A close-up photograph.
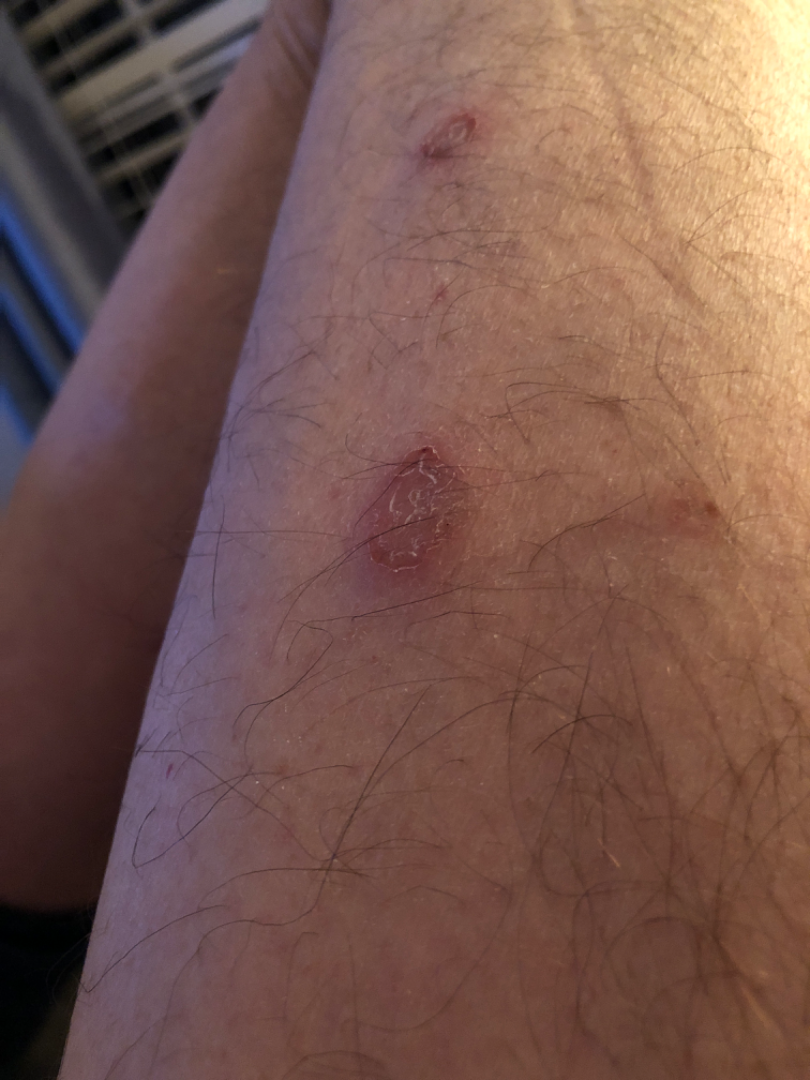Case summary:
- skin tone — Fitzpatrick skin type III
- differential diagnosis — Eczema (weight 0.41); Impetigo (weight 0.41); Psoriasis (weight 0.18)